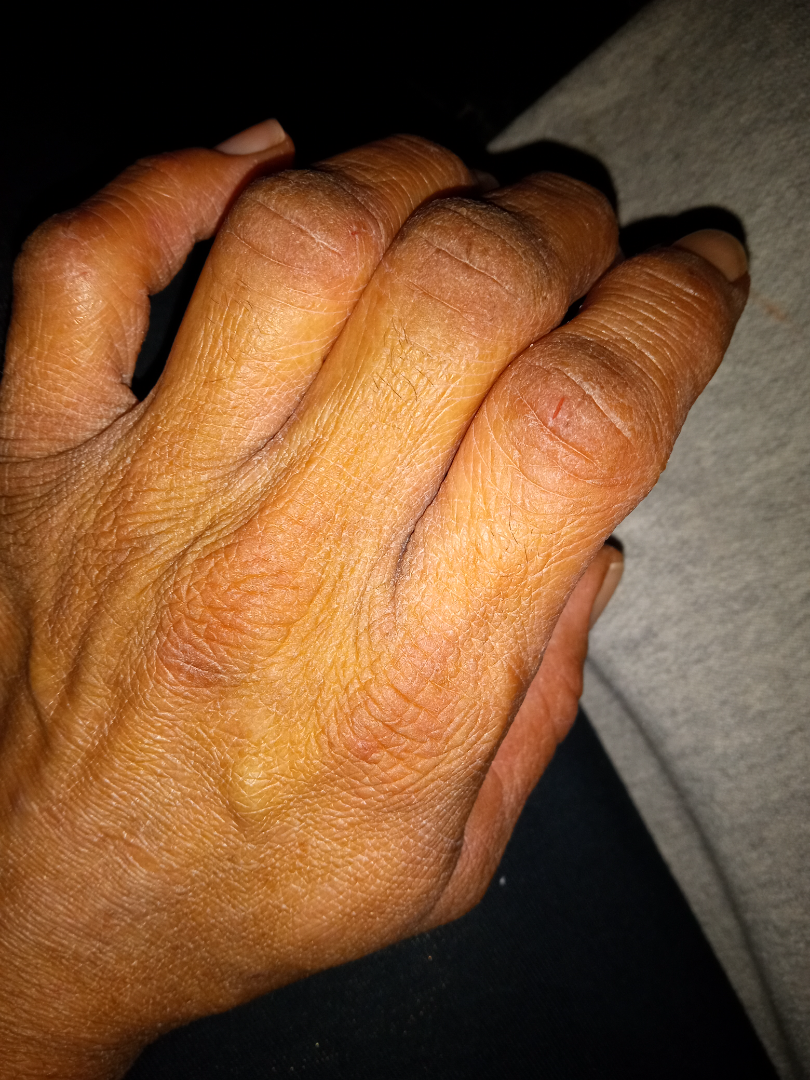The contributor reports the condition has been present for one to four weeks.
The photograph was taken at a distance.
The affected area is the back of the hand.
The lesion is associated with pain, burning and itching.
On remote review of the image: Eczema (55%); Irritant Contact Dermatitis (27%); Xerosis (18%).